A male patient aged 76 — 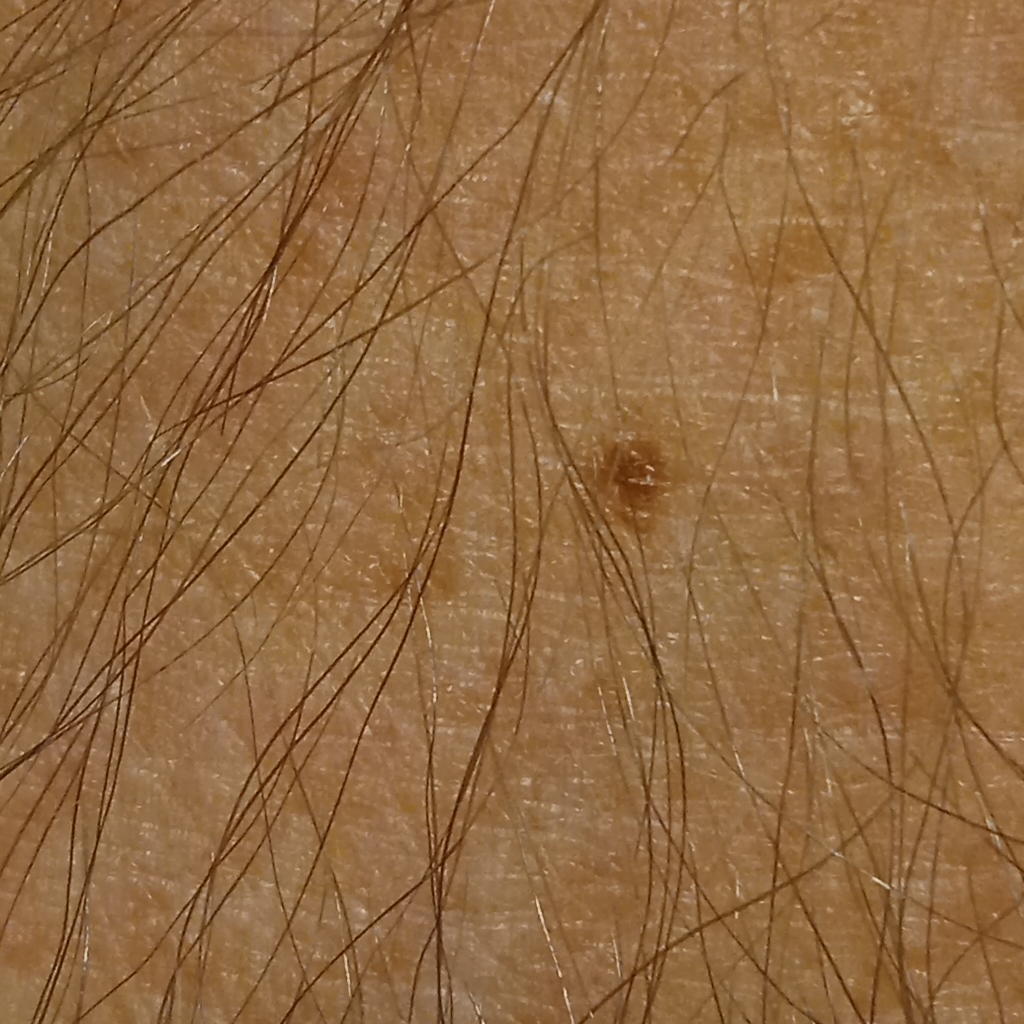The lesion involves an arm.
The lesion measures approximately 8.2 mm.
The dermatologists' assessment was a melanocytic nevus.